The photograph is a close-up of the affected area; the affected area is the head or neck; the patient is a male aged 40–49:
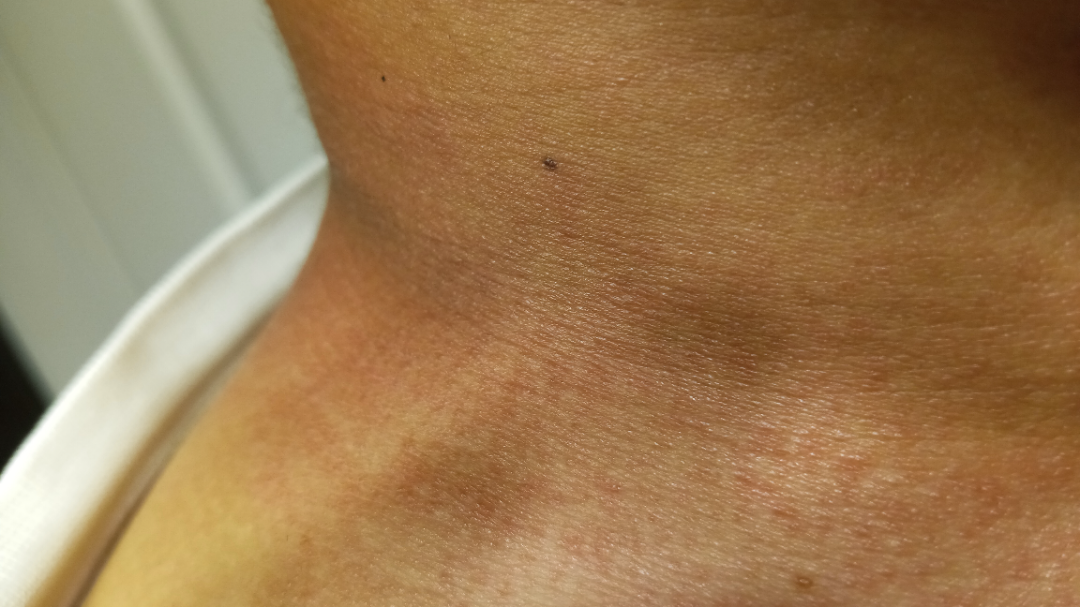{"differential": {"tied_lead": ["Photodermatitis", "Allergic Contact Dermatitis"], "unlikely": ["Eczema"]}}